The affected area is the front of the torso; the photo was captured at an angle; female subject, age 30–39 — 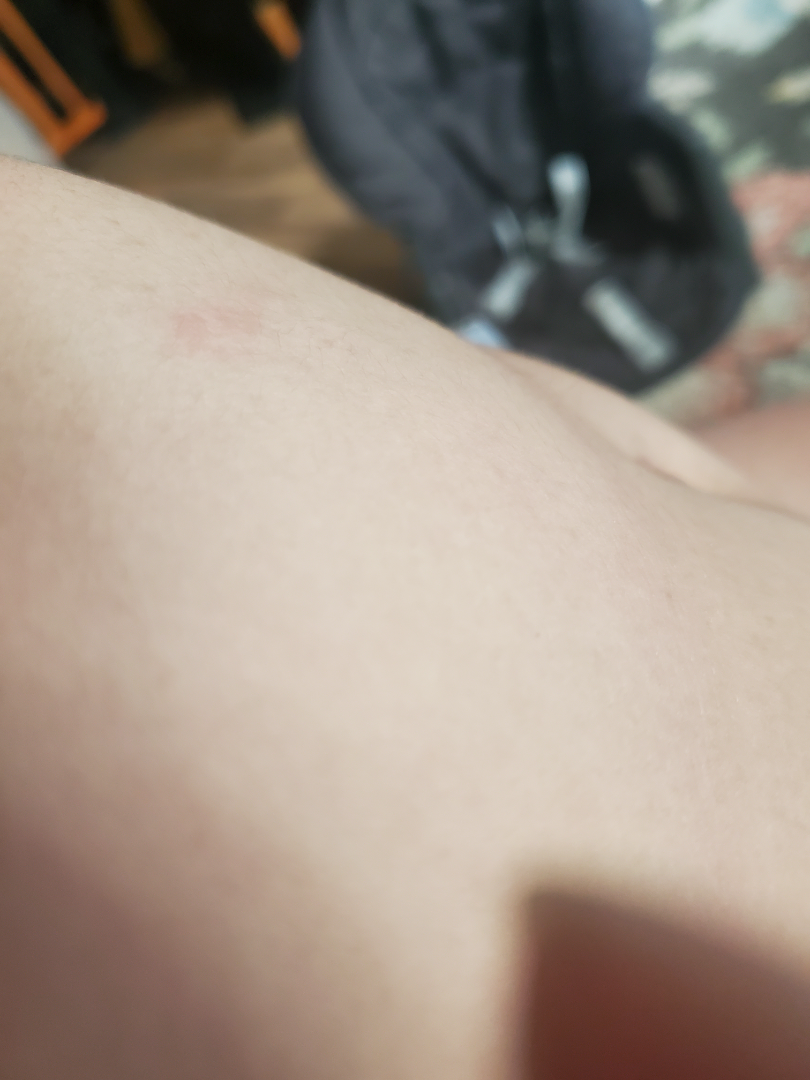assessment — not assessable; lesion symptoms — itching; history — about one day; self-categorized as — a rash.